Contact-polarized dermoscopy of a skin lesion.
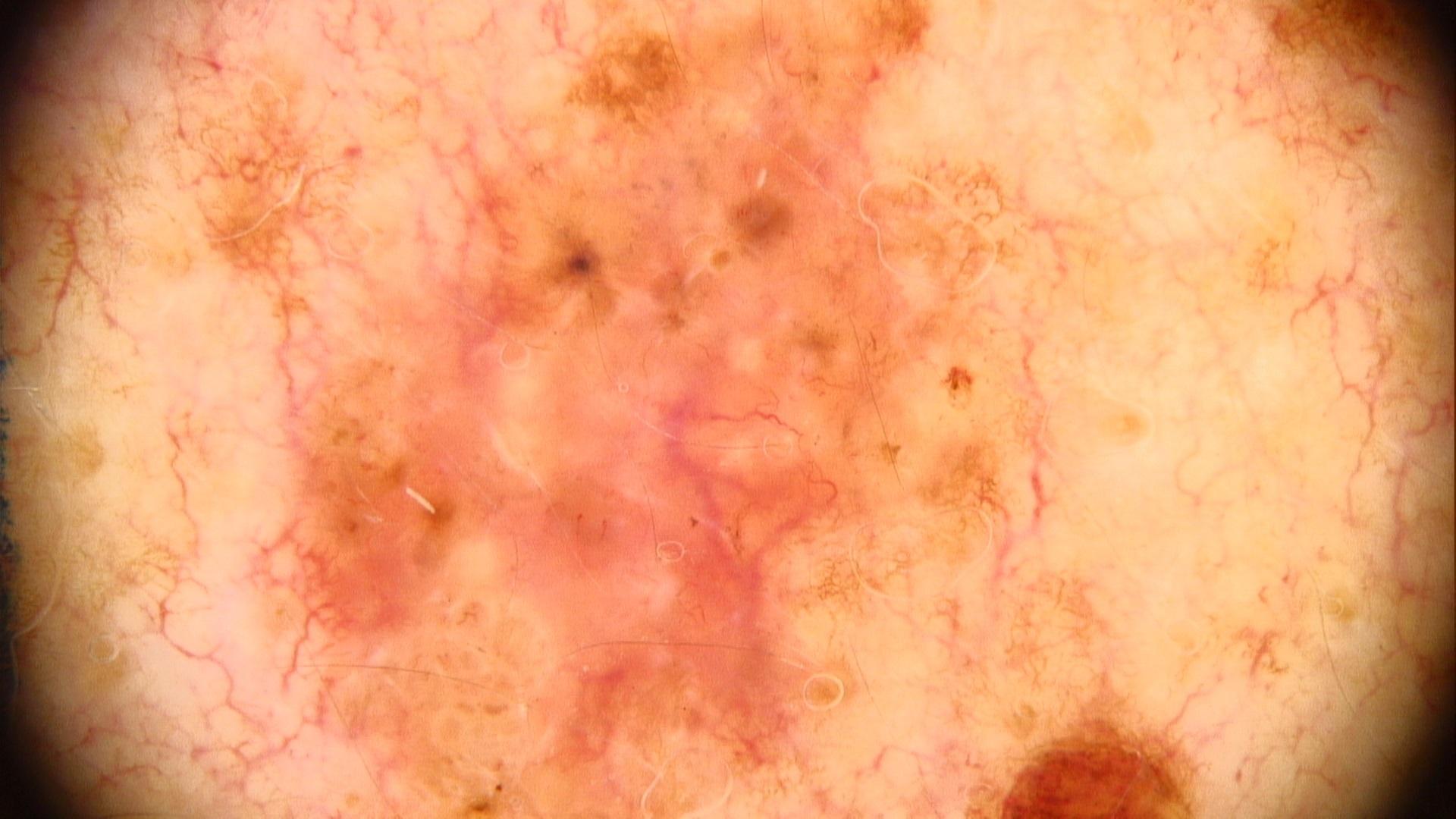  lesion_location:
    region: the trunk
  diagnosis:
    name: Basal cell carcinoma
    malignancy: malignant
    confirmation: histopathology
    lineage: adnexal